A dermoscopic close-up of a skin lesion.
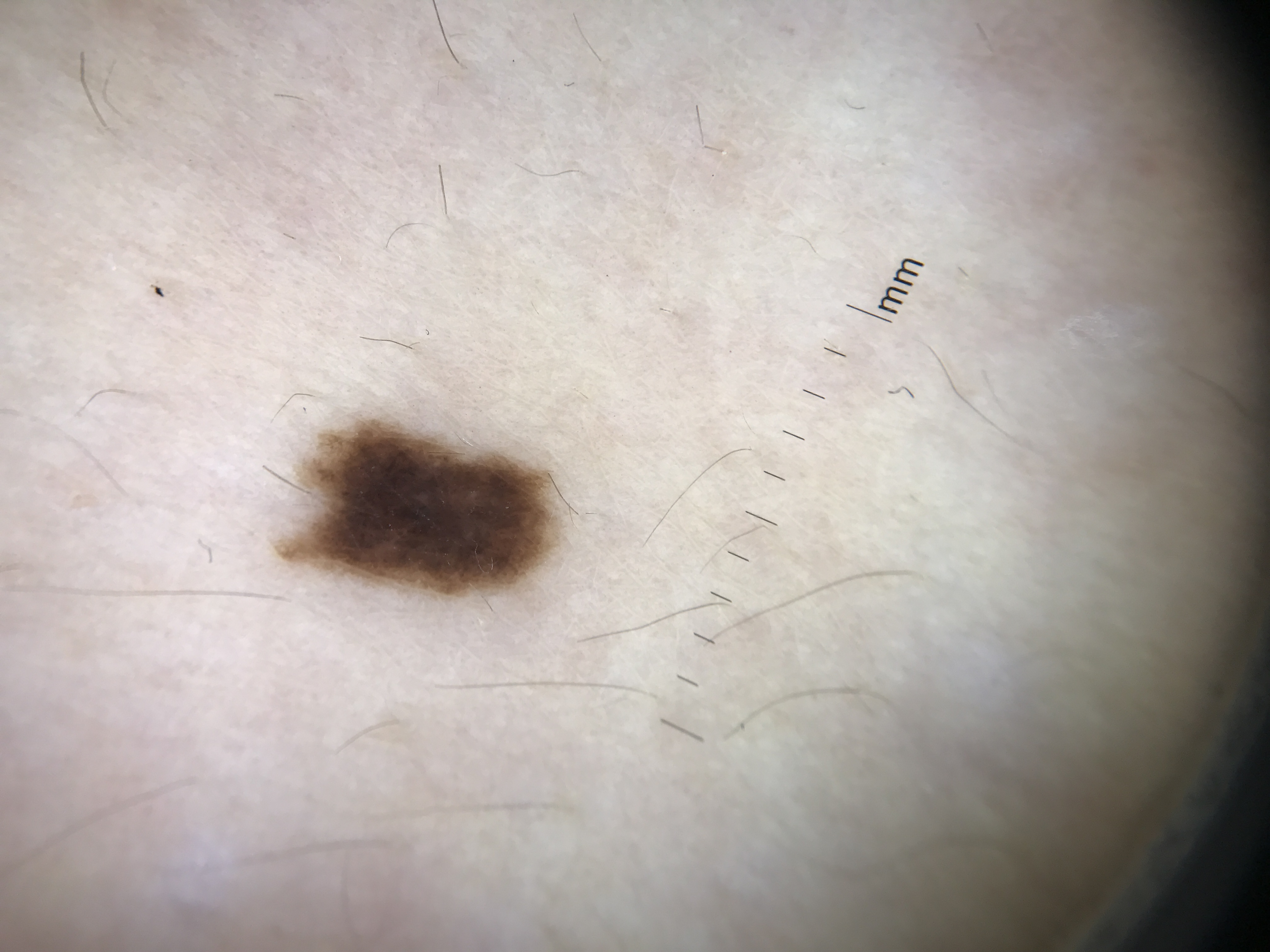label=dysplastic junctional nevus (expert consensus).